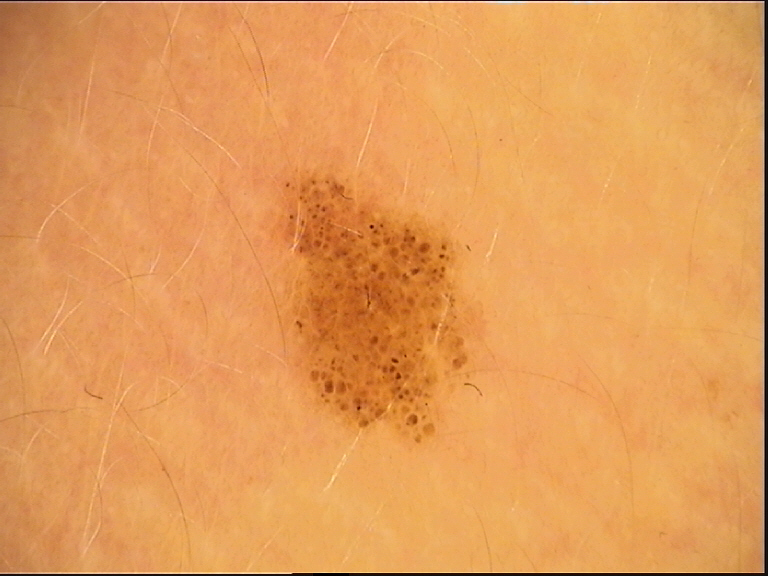A skin lesion imaged with a dermatoscope. Classified as a banal lesion — a junctional nevus.